A male subject in their late 60s:
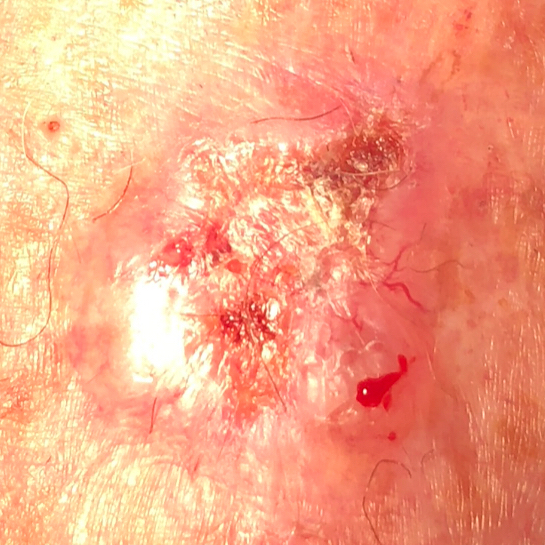anatomic site = a forearm
symptoms = elevation, pain, itching, growth, bleeding / no change in appearance
diagnostic label = basal cell carcinoma (biopsy-proven)